A dermatoscopic image of a skin lesion. A male subject aged around 20 — 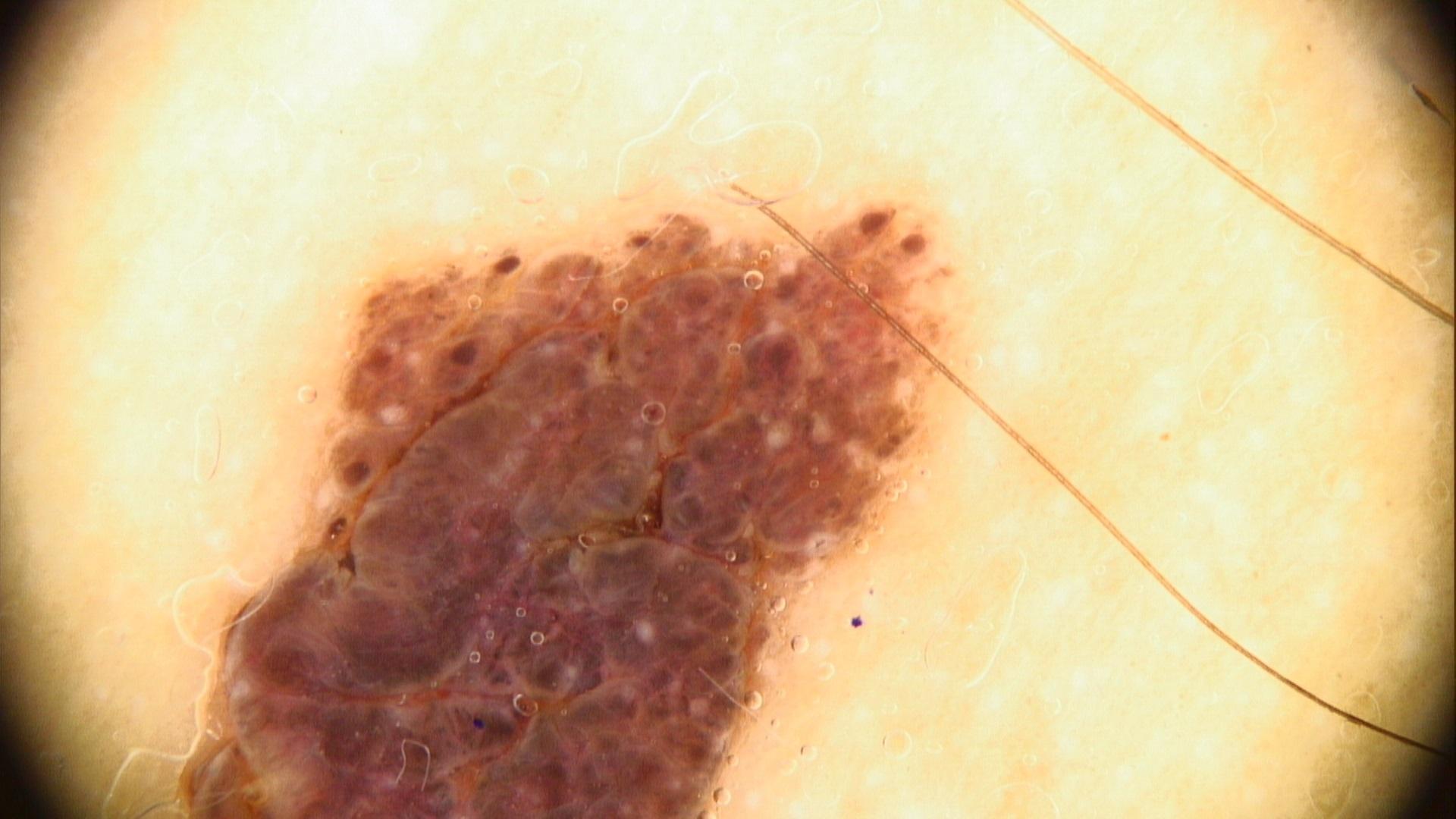Clinical context:
The lesion was found on the trunk.
Conclusion:
The clinical impression was a nevus.